A close-up photograph — 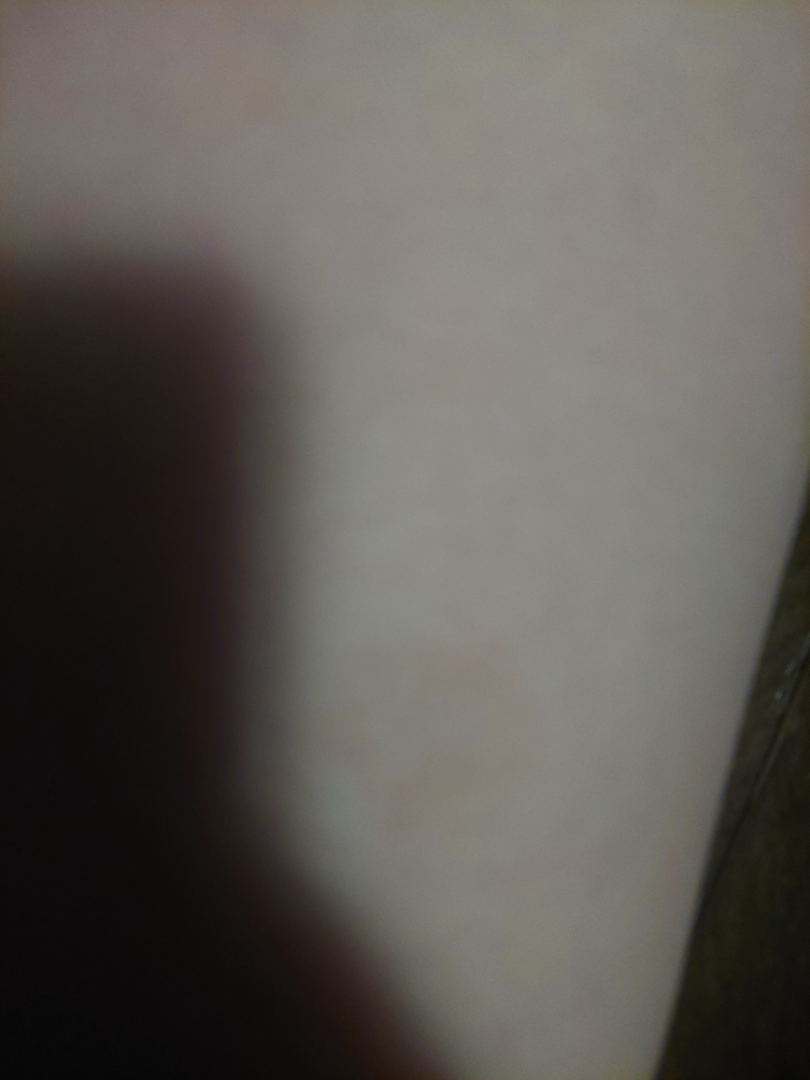Review:
The skin condition could not be confidently assessed from this image.